By self-report, a history of sunbed use and no personal history of cancer · collected as part of a research study, without a referral diagnosis · the patient says their skin reddens with sun exposure · a skin lesion imaged with a dermatoscope: 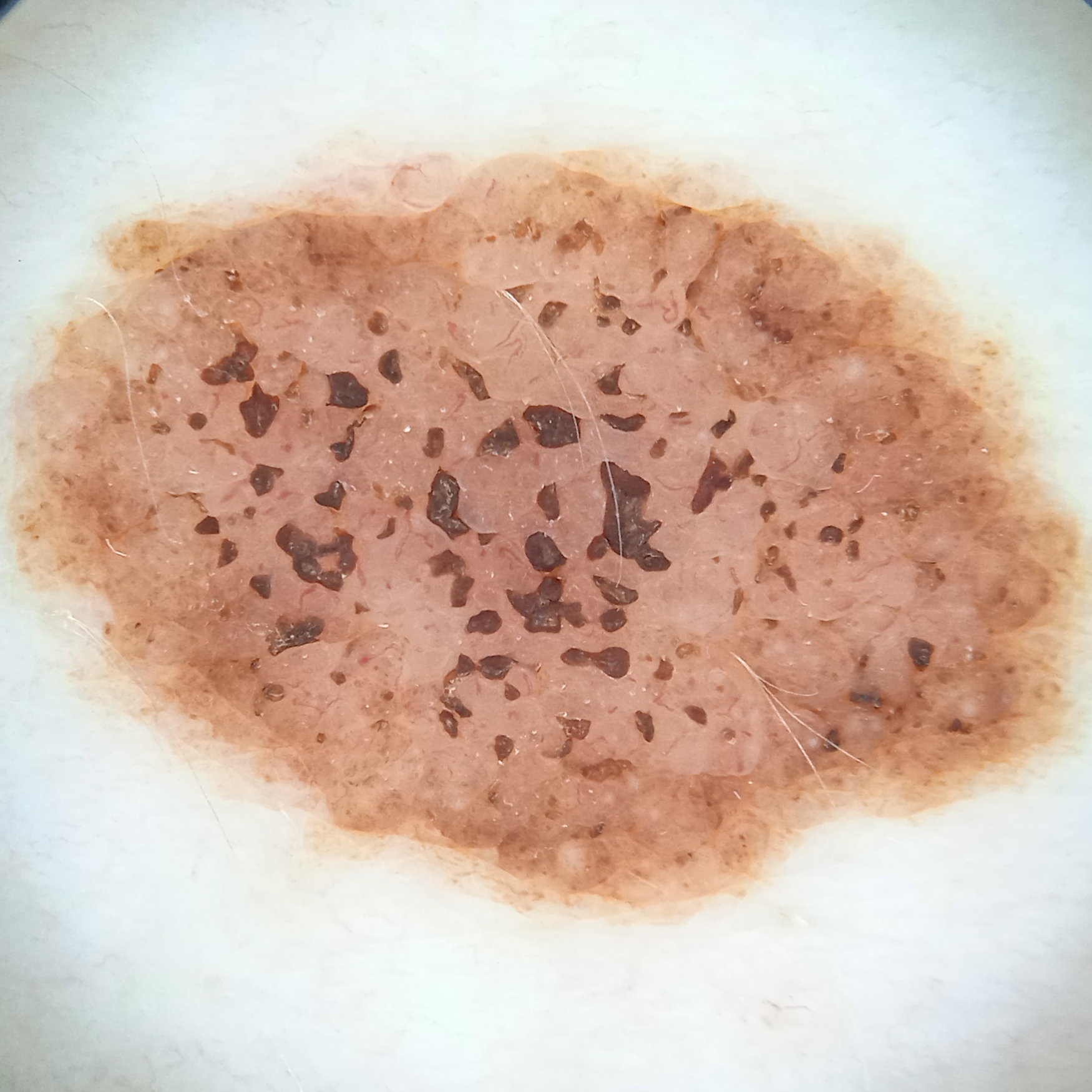Q: Where is the lesion?
A: the torso
Q: Lesion size?
A: 12.1 mm
Q: What was the diagnosis?
A: melanocytic nevus (dermatologist consensus)